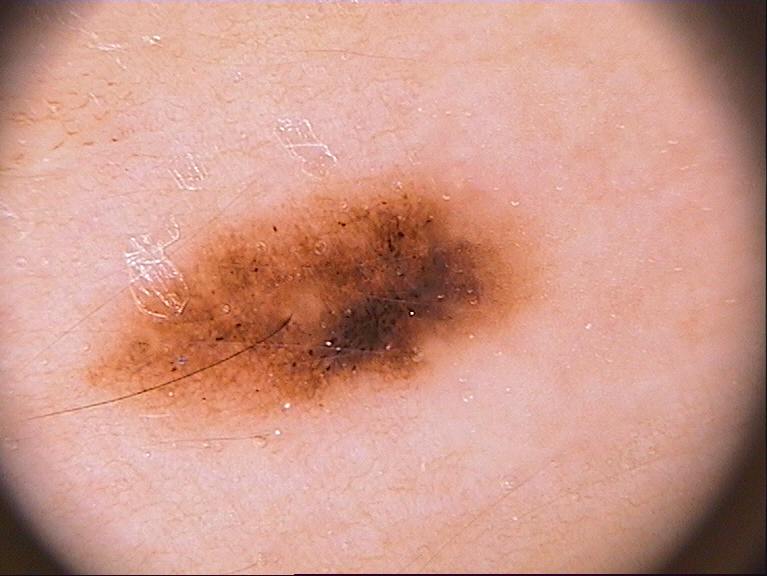A dermatoscopic image of a skin lesion.
The subject is female.
As (left, top, right, bottom), the visible lesion spans [82, 166, 564, 435].
Dermoscopic examination shows pigment network.
A moderately sized lesion.
Expert review diagnosed this as a melanocytic nevus.